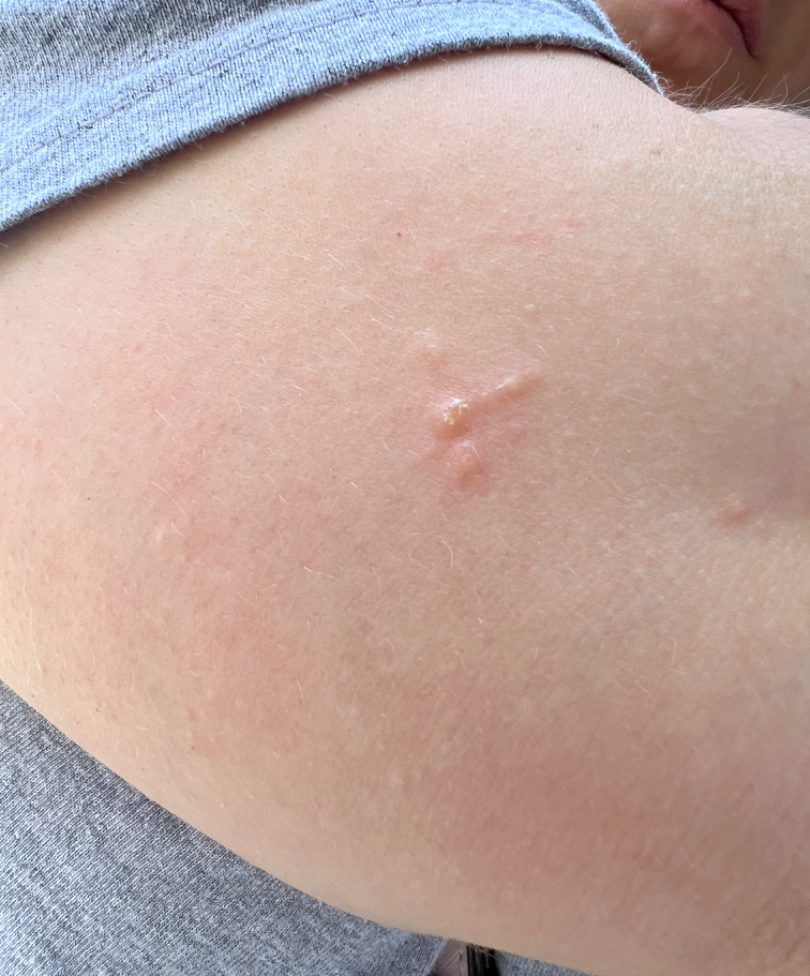Impression: The dermatologist could not determine a likely condition from the photograph alone. History: The lesion involves the arm. This is a close-up image. Self-categorized by the patient as a rash. The patient reports itching. The lesion is described as raised or bumpy.